A dermoscopic photograph of a skin lesion: 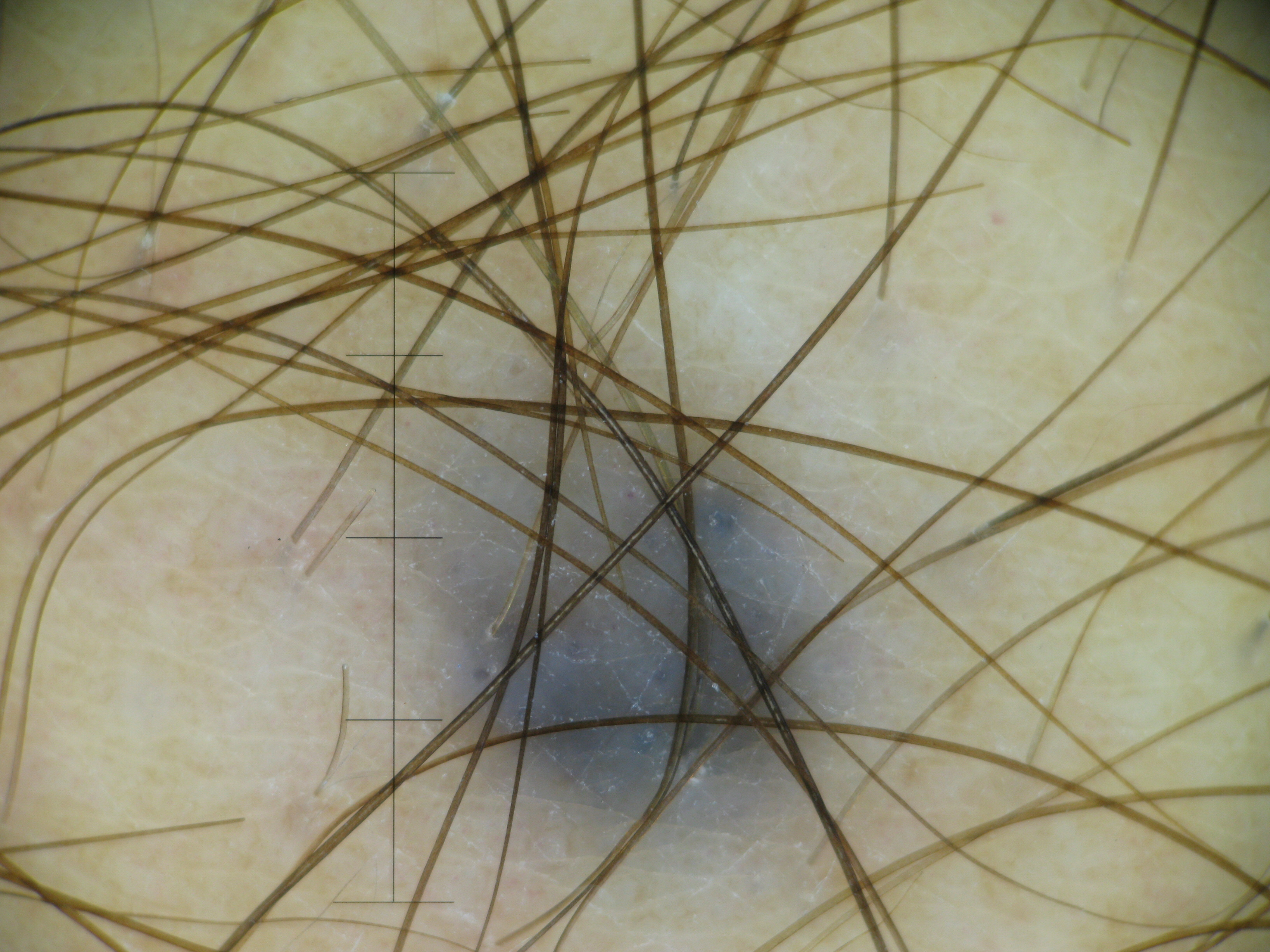<case>
<lesion_type>
<main_class>banal</main_class>
<pattern>dermal</pattern>
</lesion_type>
<diagnosis>
<name>blue nevus</name>
<code>bdb</code>
<malignancy>benign</malignancy>
<super_class>melanocytic</super_class>
<confirmation>expert consensus</confirmation>
</diagnosis>
</case>